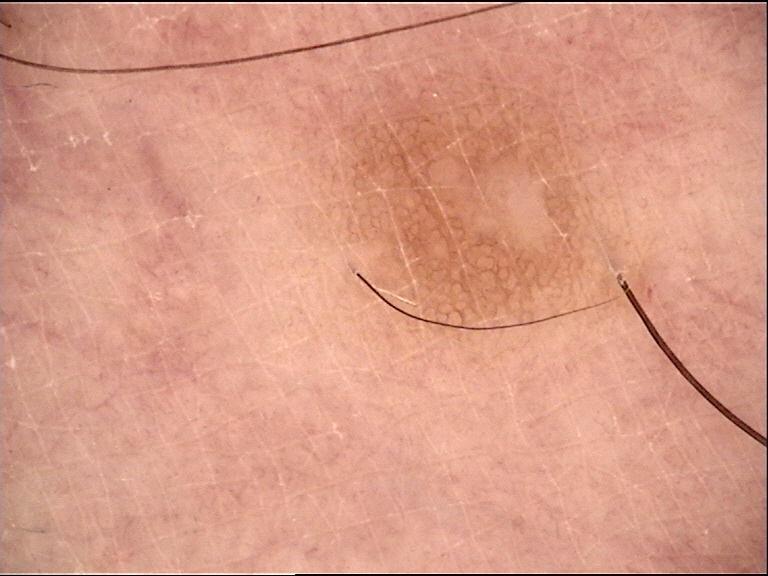A dermoscopic photograph of a skin lesion. This is a fibro-histiocytic lesion. The diagnosis was a benign lesion — a dermatofibroma.